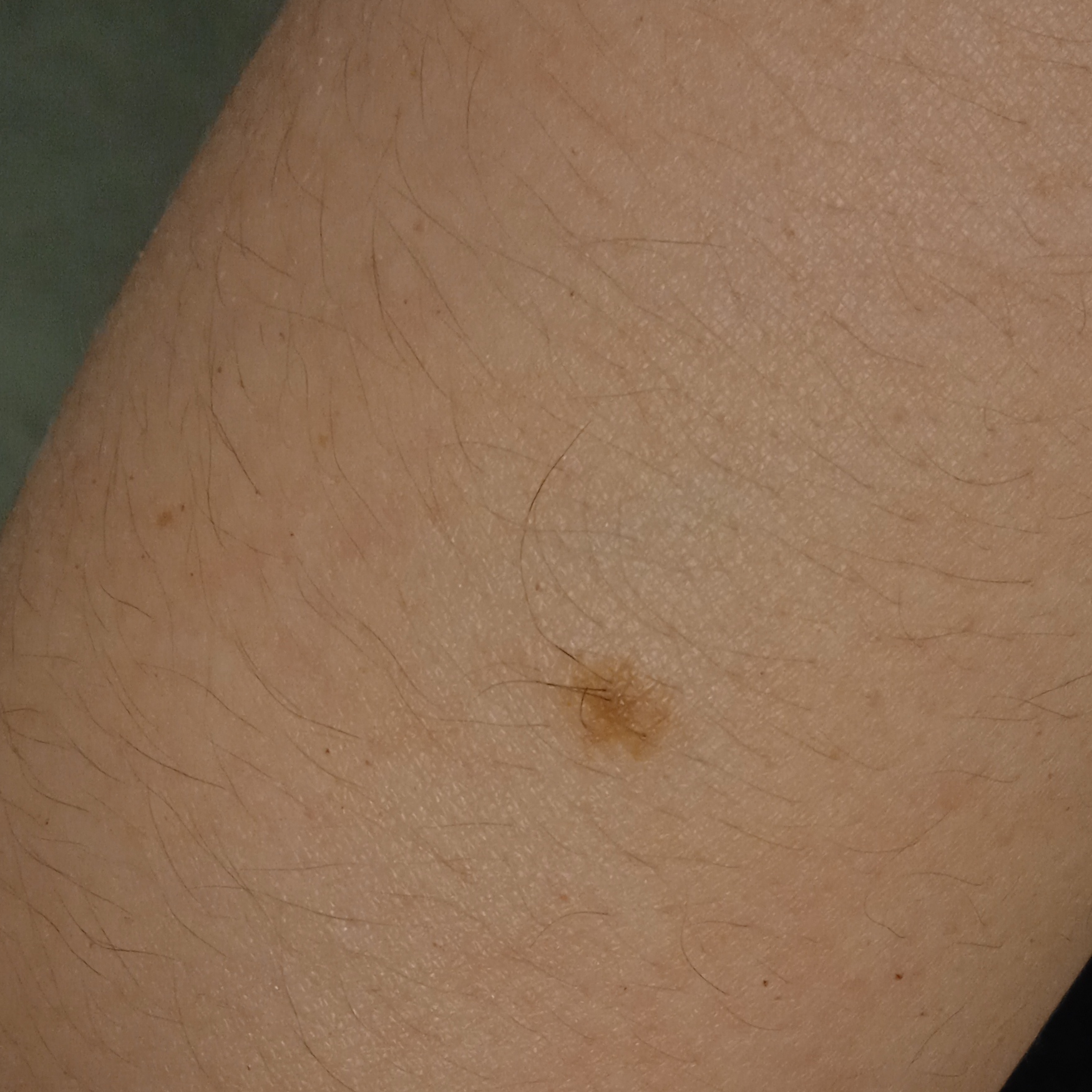The patient says their skin reddens painfully with sun exposure.
Imaged for a research study, with no referral diagnosis recorded.
A clinical photograph of a skin lesion.
The lesion is on an arm.
The lesion measures approximately 5.8 mm.
The lesion was assessed as a melanocytic nevus.